A clinical photograph of a skin lesion — 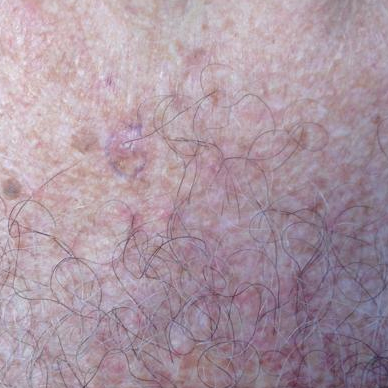Q: Any reported symptoms?
A: itching
Q: What is the diagnosis?
A: actinic keratosis (clinical consensus)